A dermoscopic photograph of a skin lesion.
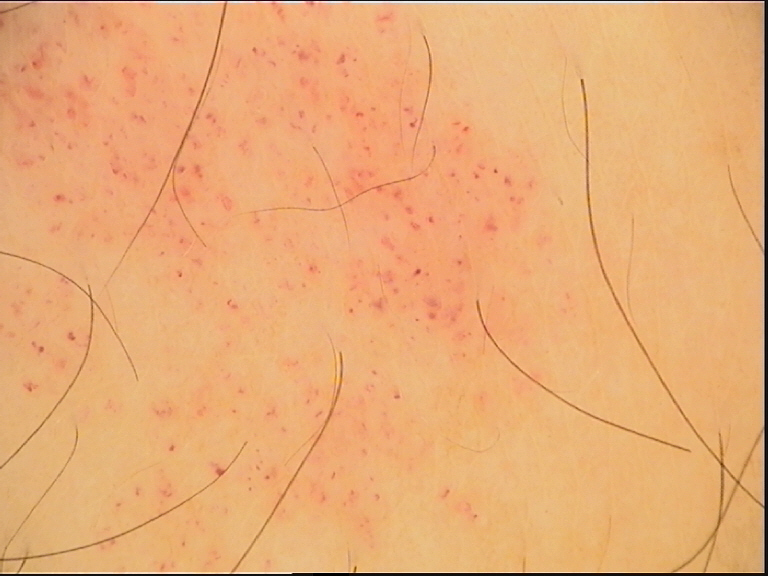Impression: Labeled as a vascular, benign lesion — a hemangioma.